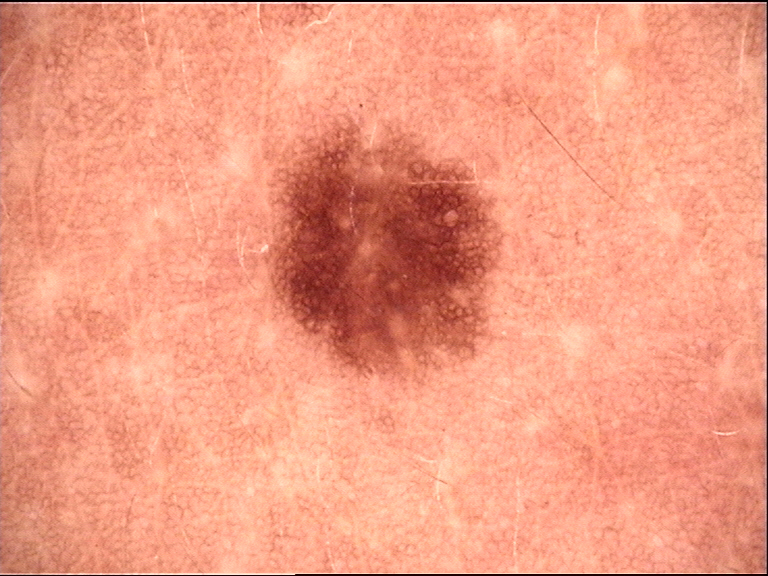| feature | finding |
|---|---|
| diagnosis | dysplastic junctional nevus (expert consensus) |